A dermoscopy image of a single skin lesion.
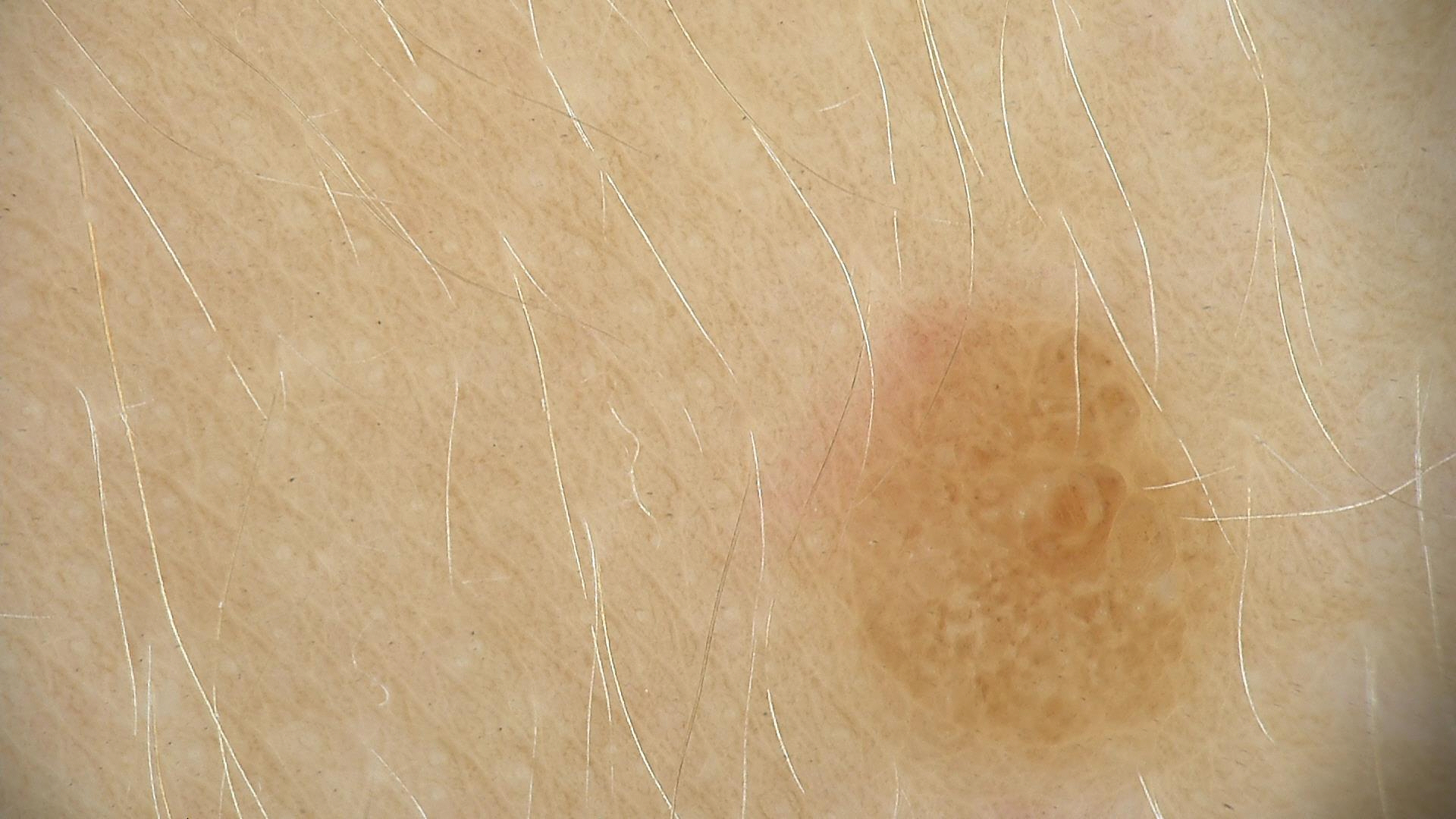Conclusion: Diagnosed as a benign lesion — a dysplastic junctional nevus.